A skin lesion imaged with a dermatoscope, the patient is a male in their 80s:
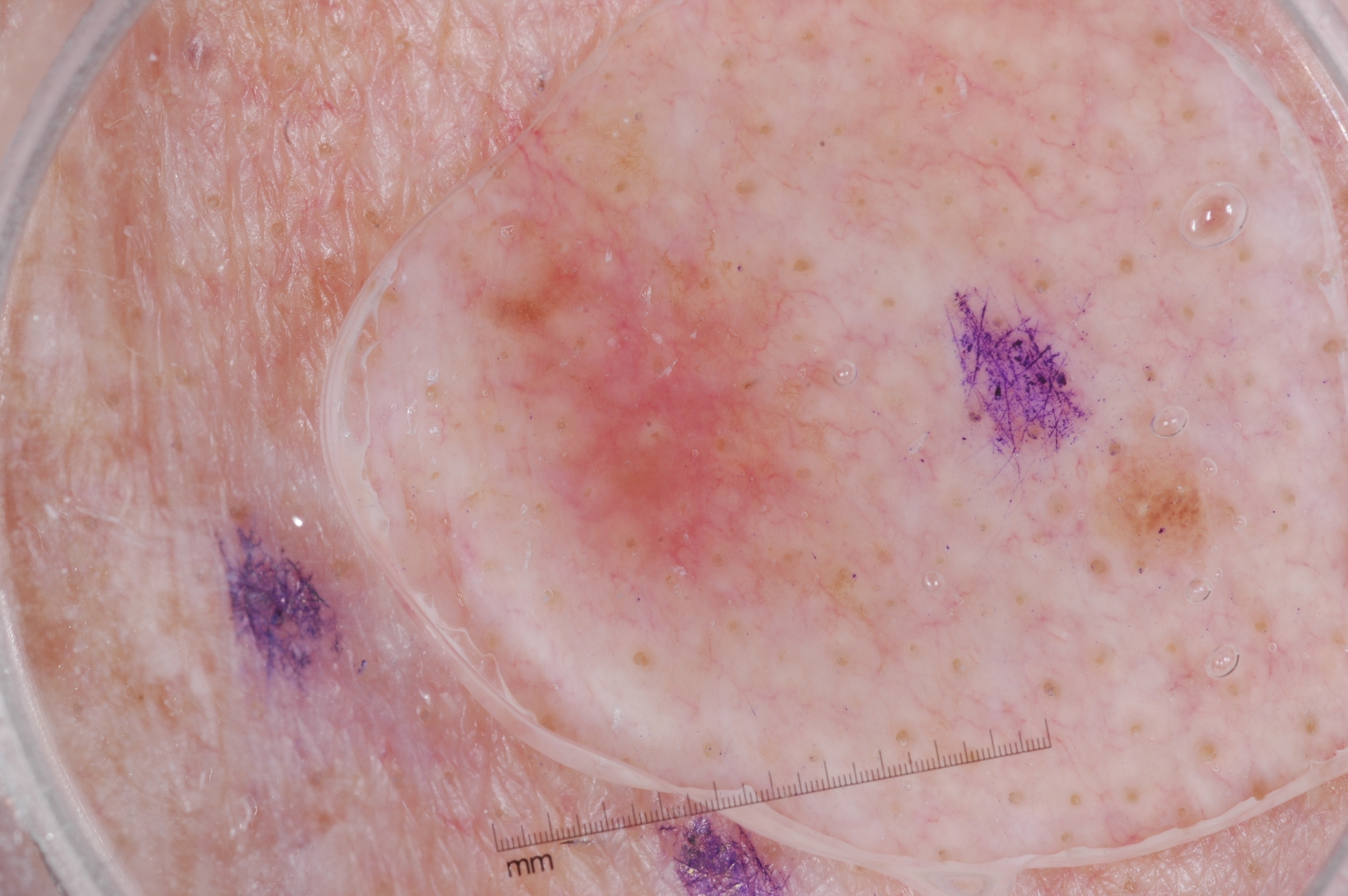Notes:
– extent — moderate
– features — milia-like cysts; absent: negative network, streaks, and pigment network
– location — bbox(474, 168, 853, 616)
– impression — a seborrheic keratosis, a non-melanocytic (keratinocytic) lesion